The photograph is a close-up of the affected area, the affected area is the palm: 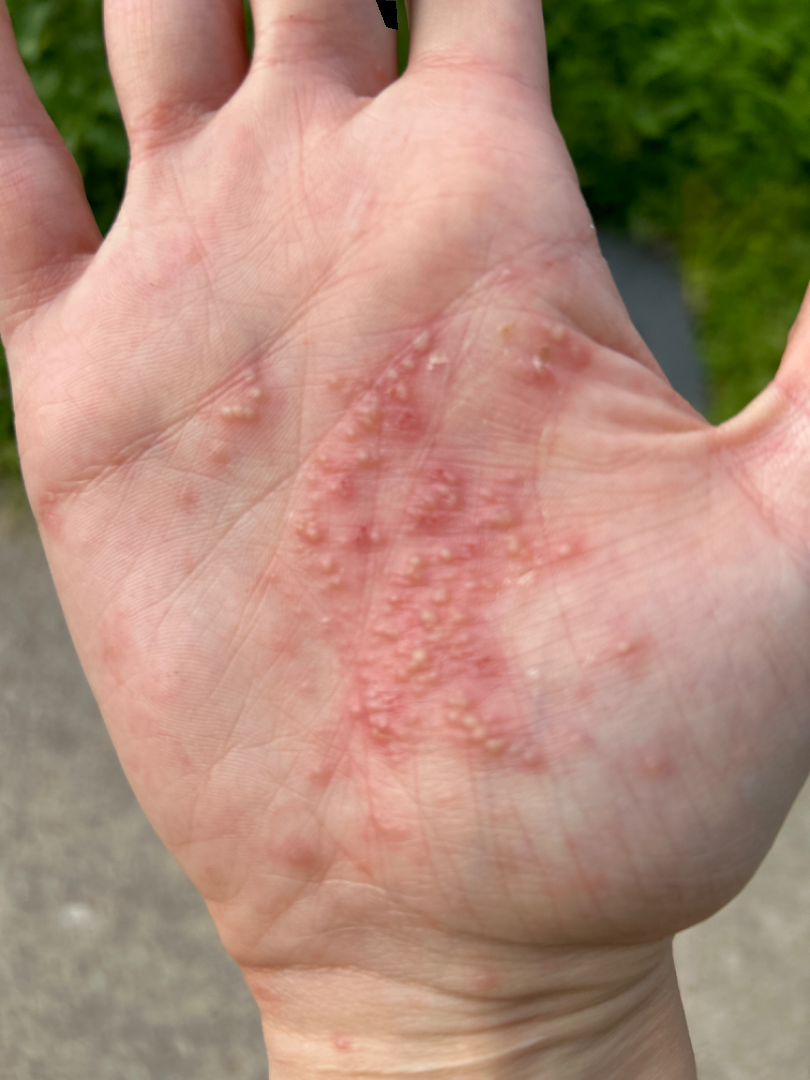{
  "assessment": "could not be assessed",
  "symptoms": [
    "enlargement",
    "bothersome appearance",
    "itching",
    "burning"
  ],
  "patient_category": "a rash",
  "systemic_symptoms": "none reported"
}